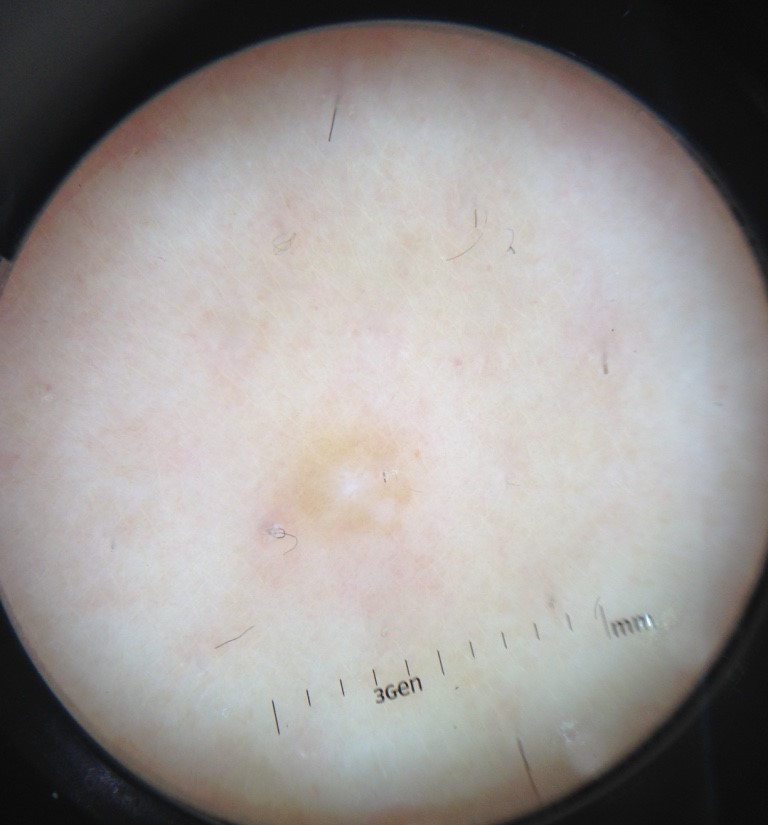{
  "image": "dermatoscopy",
  "lesion_type": {
    "main_class": "fibro-histiocytic"
  },
  "diagnosis": {
    "name": "dermatofibroma",
    "code": "df",
    "malignancy": "benign",
    "super_class": "non-melanocytic",
    "confirmation": "expert consensus"
  }
}